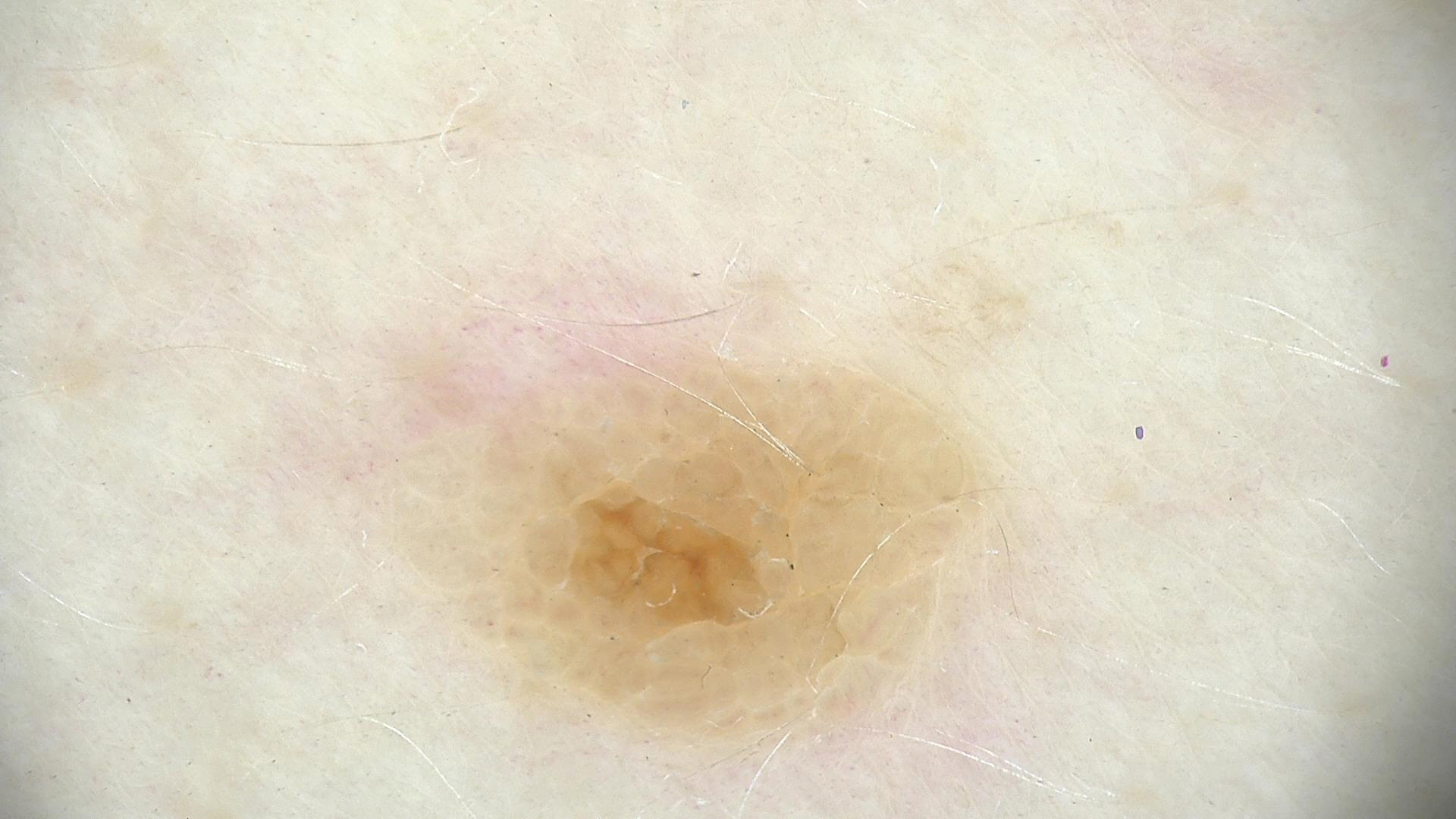A dermatoscopic image of a skin lesion. This is a keratinocytic lesion. Consistent with a benign lesion — a seborrheic keratosis.